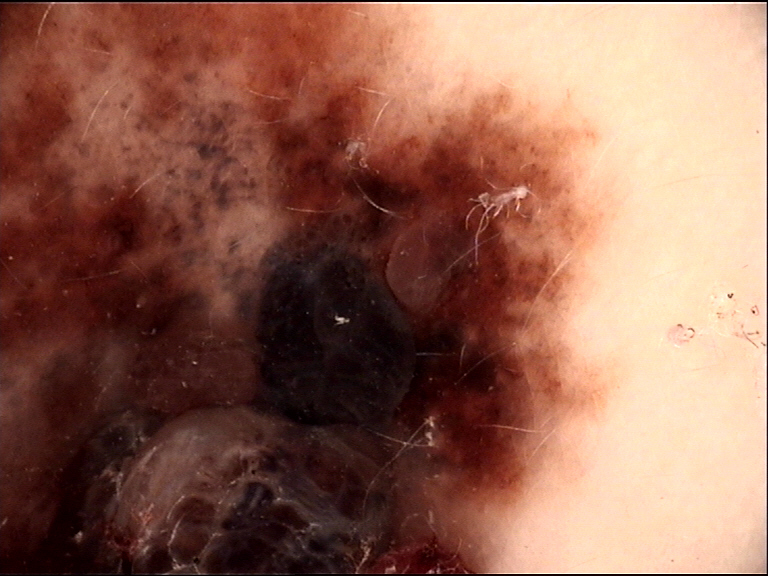Q: What kind of image is this?
A: dermatoscopy
Q: What is the diagnosis?
A: melanoma (biopsy-proven)